The referring clinician suspected basal cell carcinoma. On a questionnaire the patient reported a family history of skin cancer and a personal history of cancer. A male subject 81 years old. The patient says their skin reddens with sun exposure: 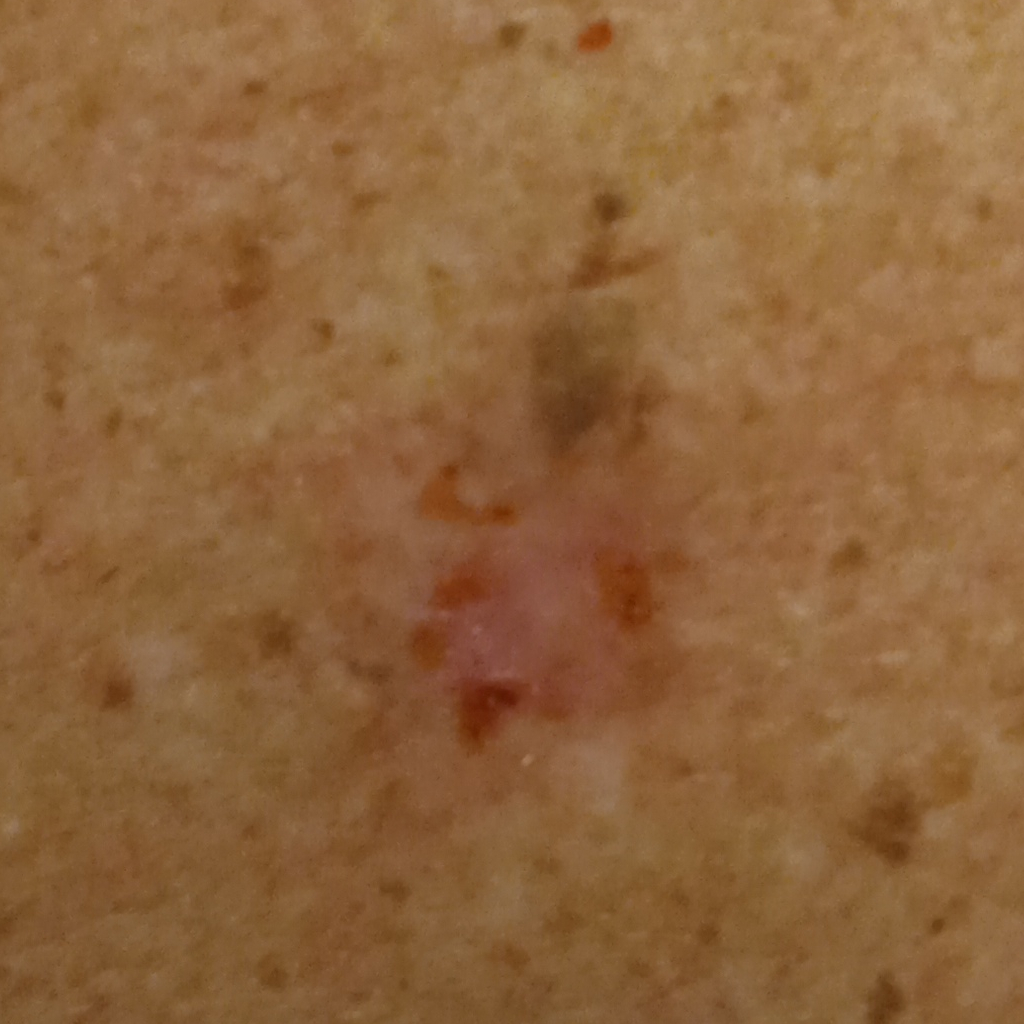Located on the back. The lesion measures approximately 12.6 mm. The biopsy diagnosis was a basal cell carcinoma, following excision, with a measured thickness of 3 mm.